A patient aged 75. A smartphone photograph of a skin lesion: 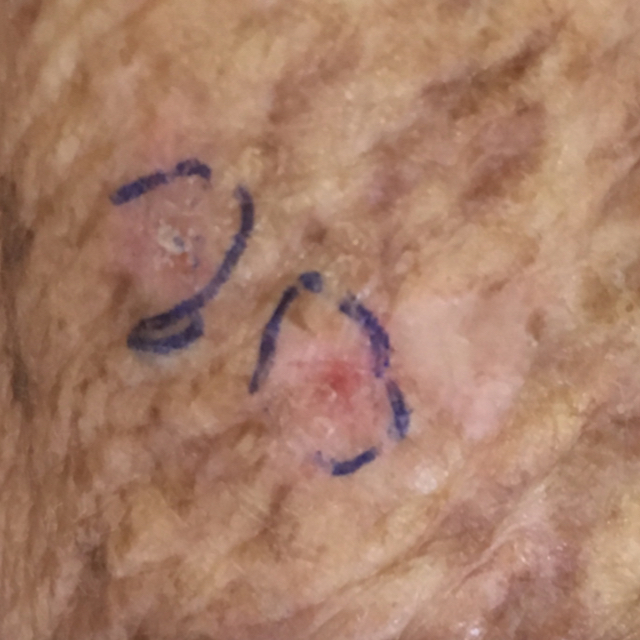| feature | finding |
|---|---|
| site | an arm |
| patient-reported symptoms | itching / no pain |
| assessment | actinic keratosis (clinical consensus) |